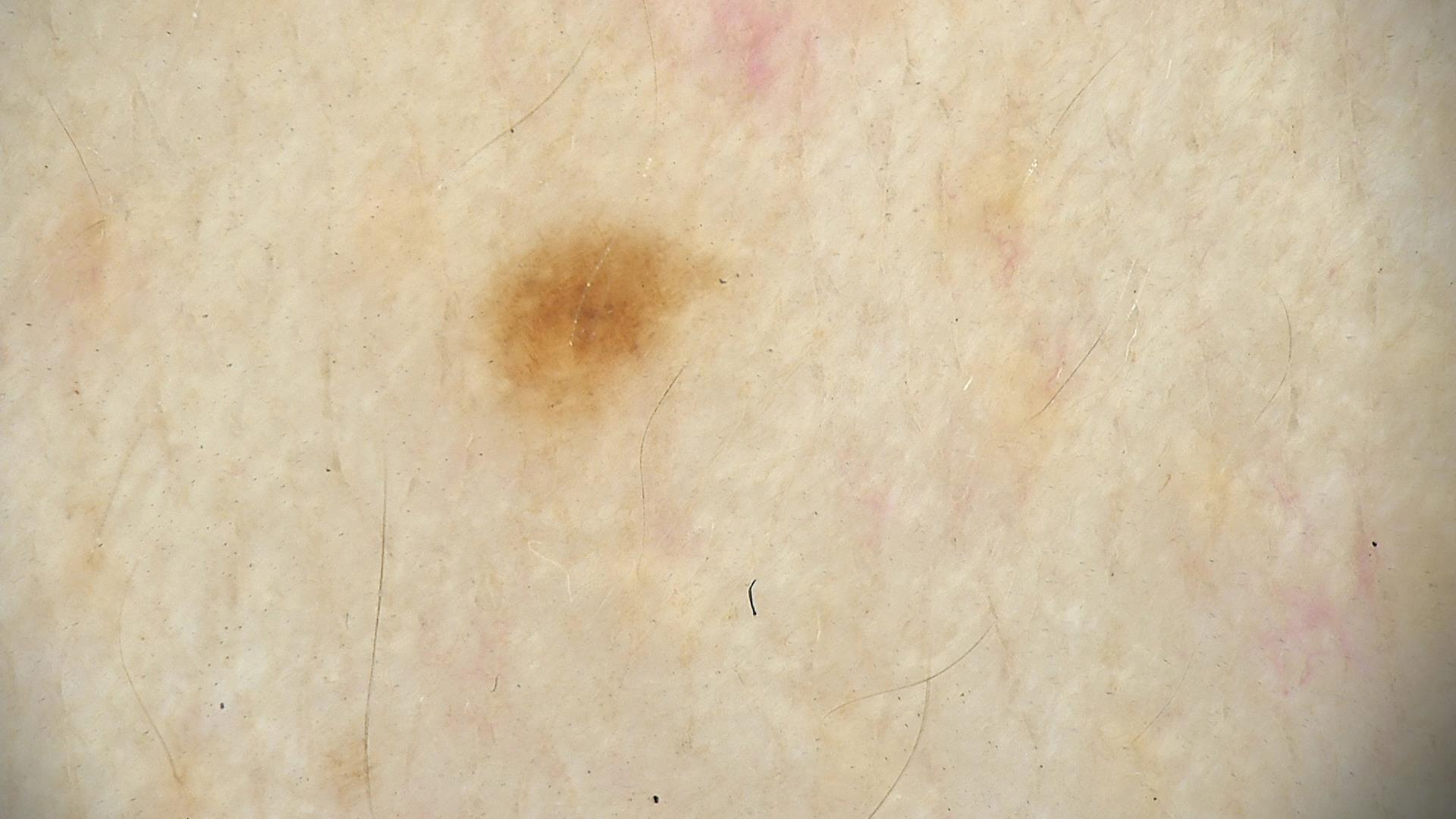Impression: Consistent with a benign lesion — a dysplastic junctional nevus.